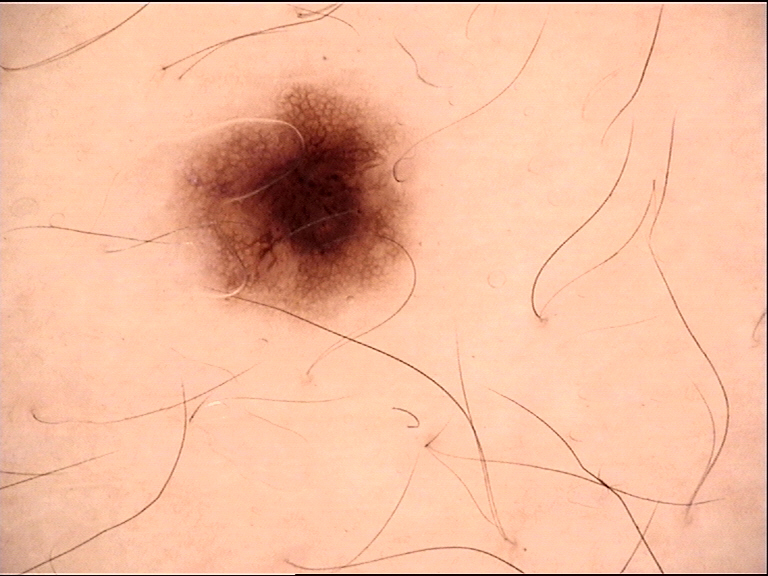Labeled as a junctional nevus.